A dermoscopy image of a single skin lesion.
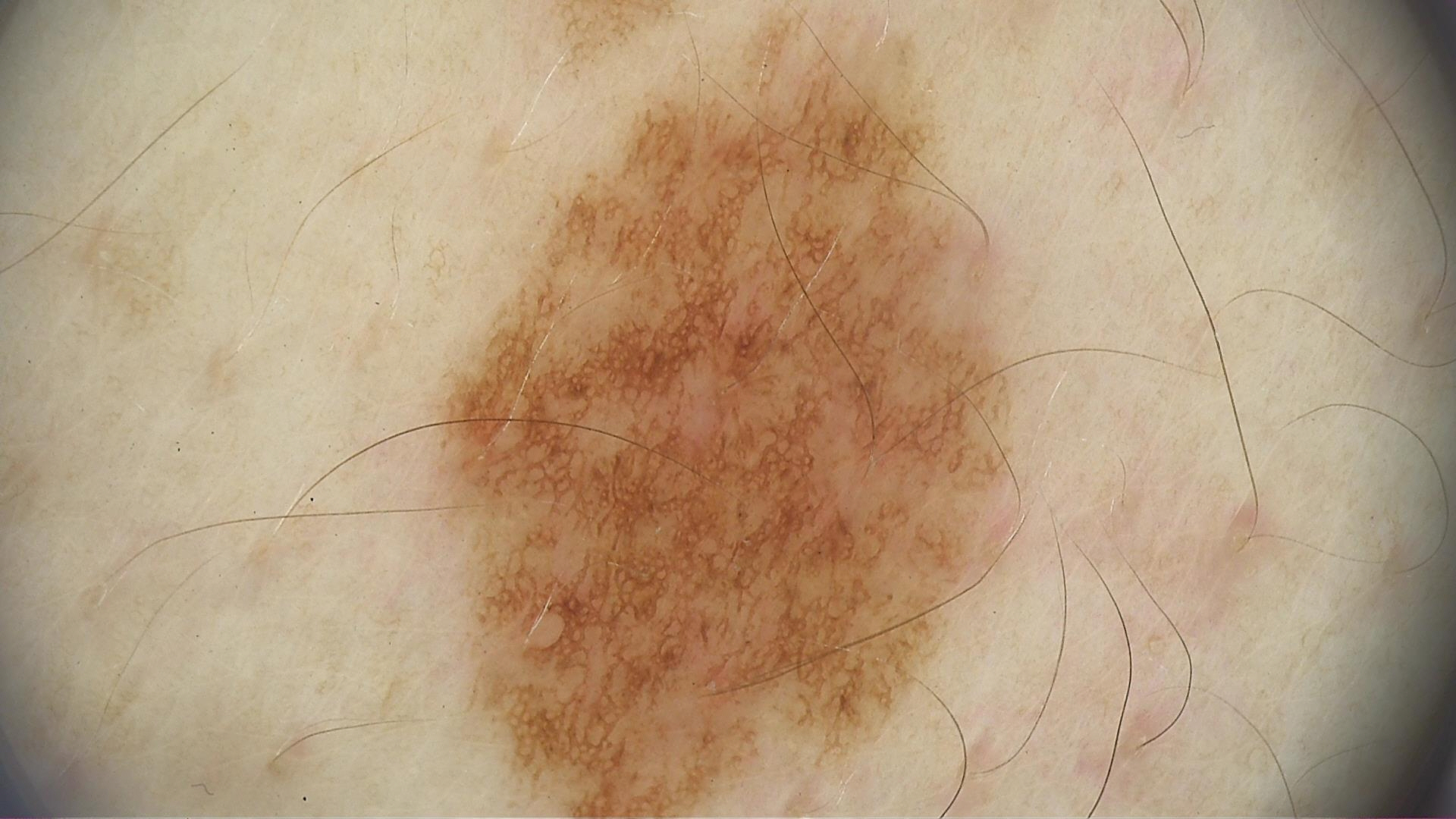Diagnosed as a dysplastic junctional nevus.